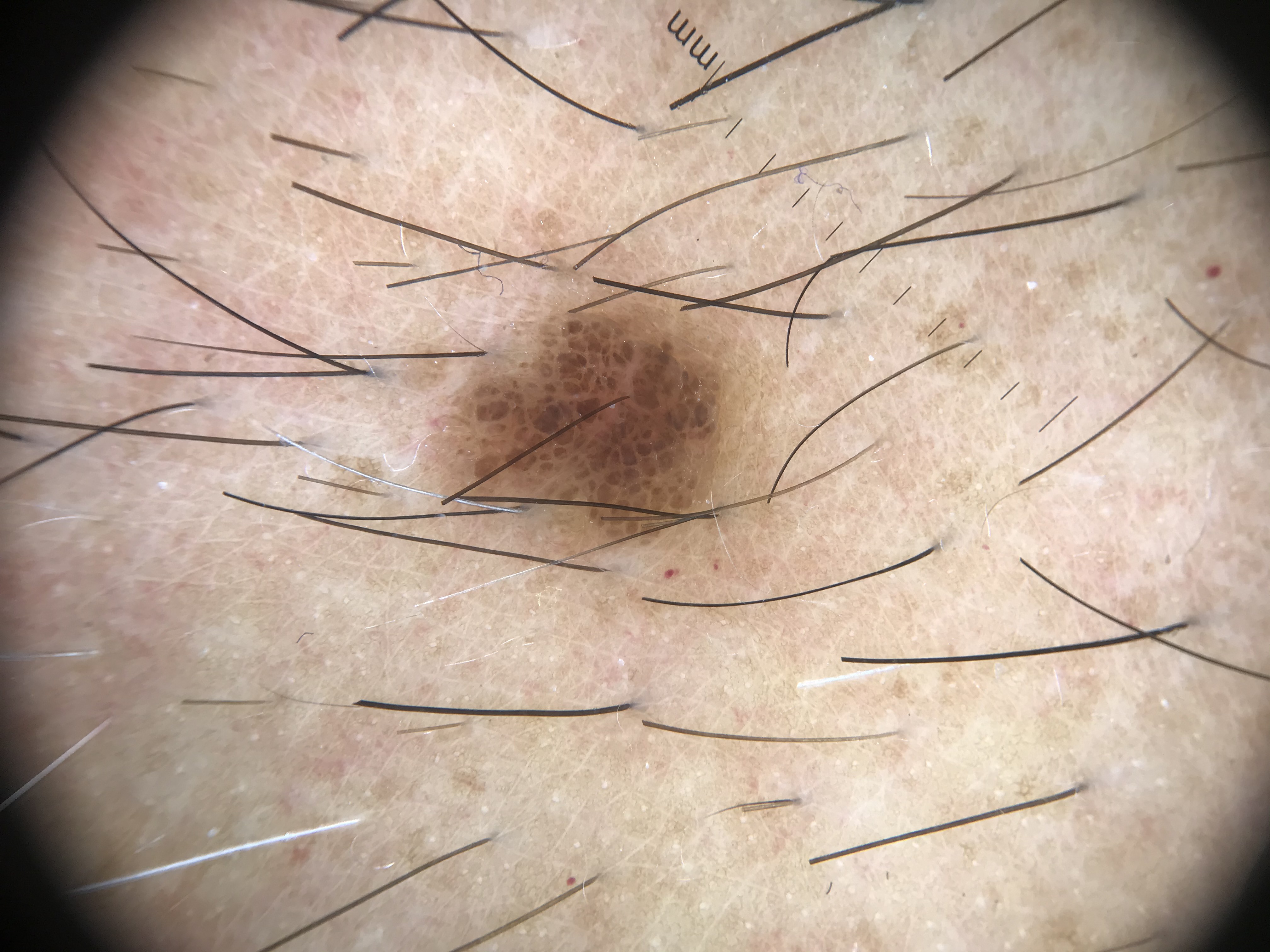modality = dermoscopy | subtype = banal | diagnosis = compound nevus (expert consensus).